Located on the arm; the patient reports itching and enlargement; the patient reports the lesion is raised or bumpy, rough or flaky and fluid-filled; present for one to four weeks; the patient is a female aged 30–39; the photo was captured at a distance; the patient considered this a rash: 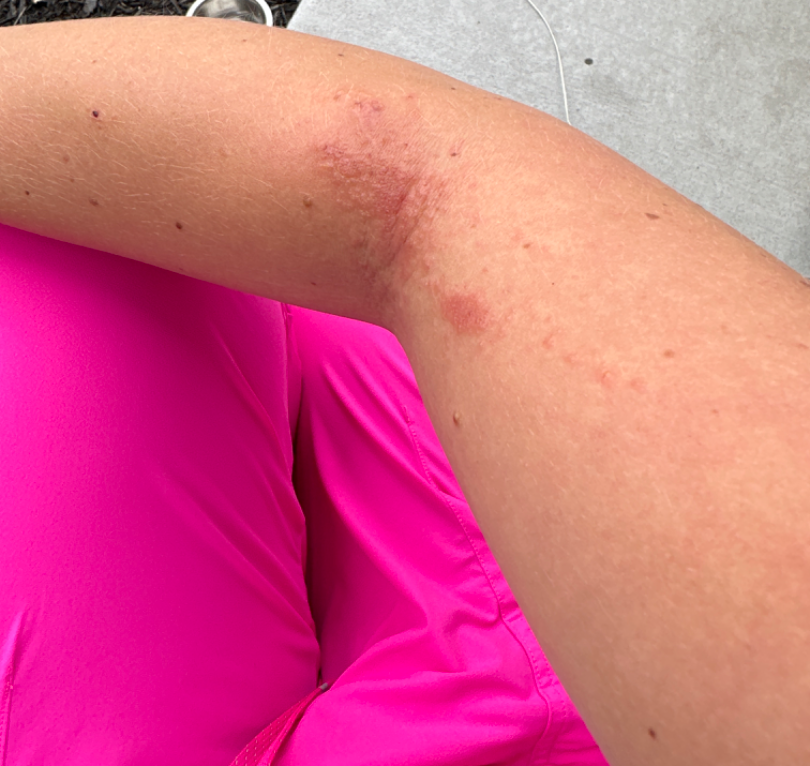| key | value |
|---|---|
| assessment | the primary impression is Eczema; also raised was Allergic Contact Dermatitis |